This is a dermoscopic photograph of a skin lesion. A male patient aged approximately 65:
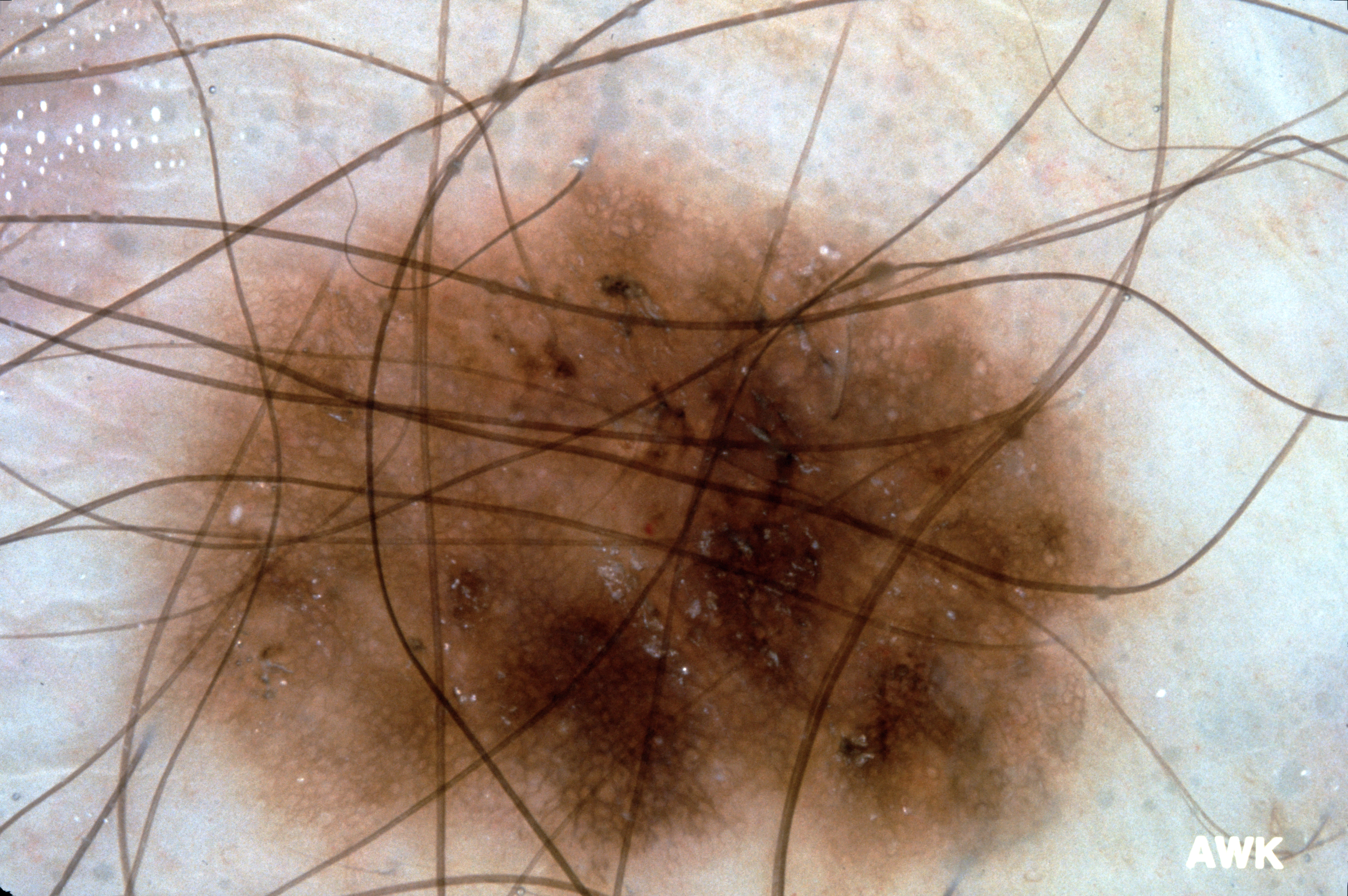| feature | finding |
|---|---|
| dermoscopic findings | pigment network |
| lesion location | x1=121 y1=56 x2=1177 y2=892 |
| impression | a melanocytic nevus |